A dermoscopic close-up of a skin lesion.
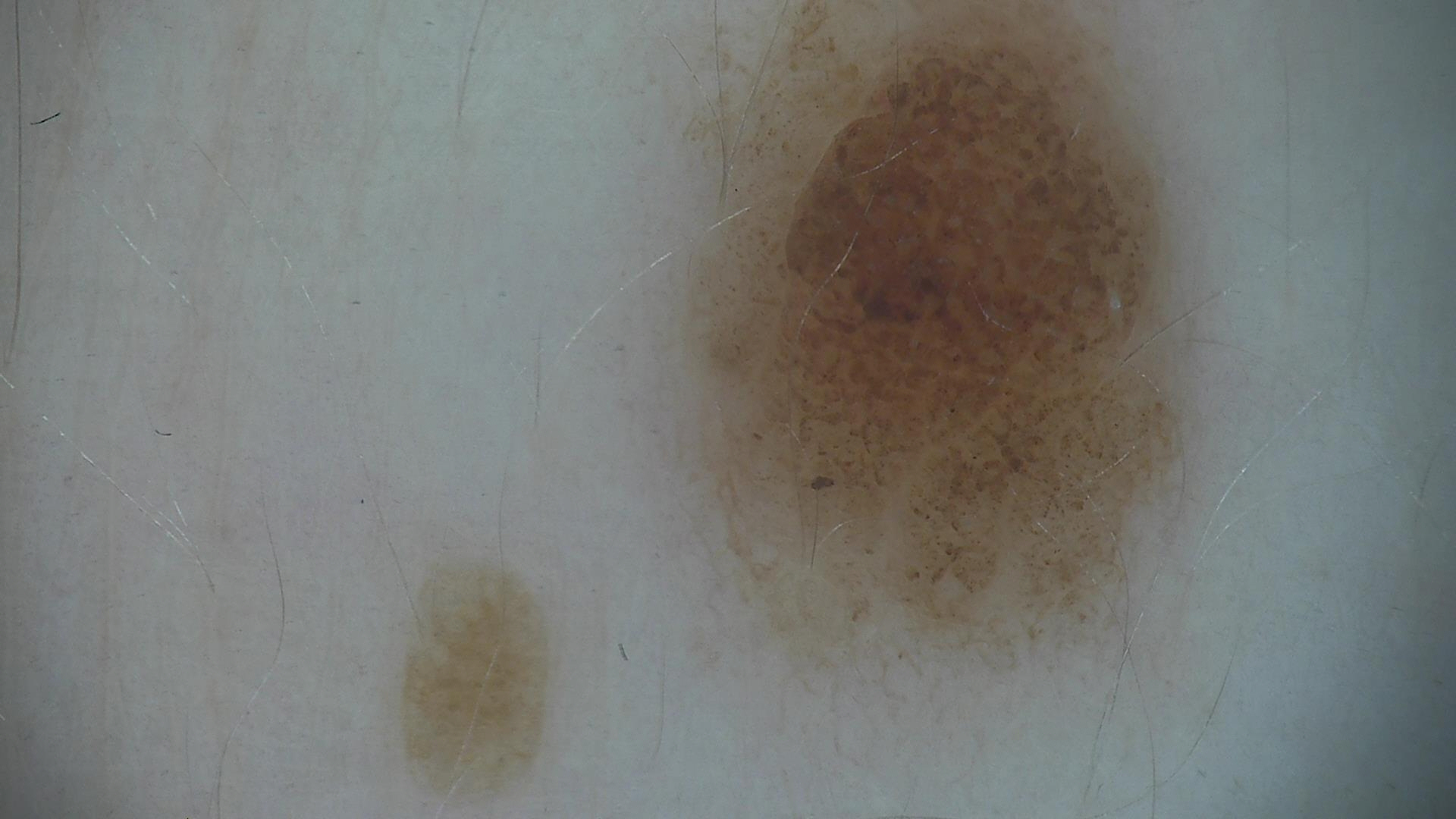diagnosis — compound nevus (expert consensus).